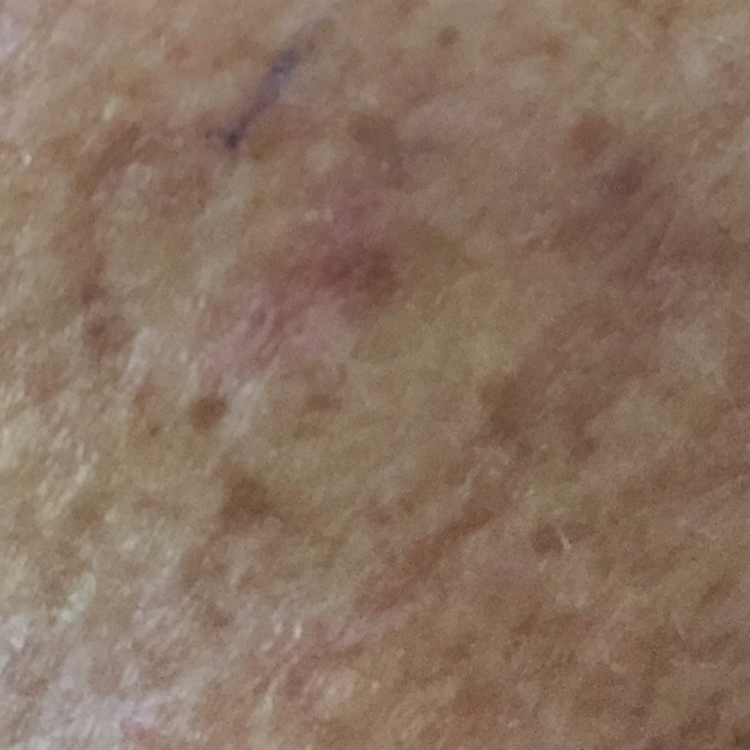patient: aged 50 | image: clinical photograph | site: the chest | diagnostic label: actinic keratosis (clinical consensus).